The affected area is the back of the hand, leg, front of the torso, head or neck and arm. This image was taken at an angle.
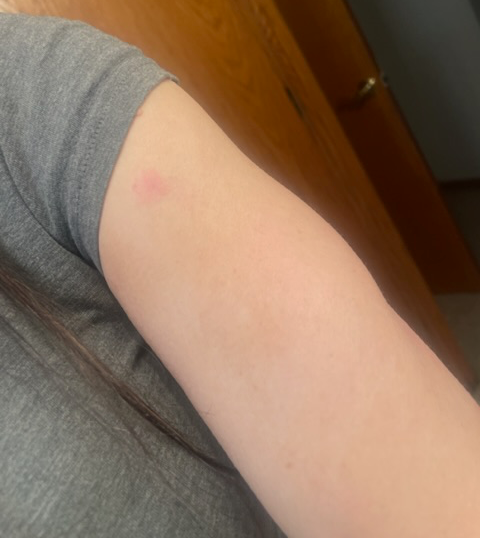The skin findings could not be characterized from the image. Texture is reported as flat and raised or bumpy. No associated systemic symptoms reported. The patient considered this skin that appeared healthy to them. Symptoms reported: enlargement, itching and bothersome appearance. Reported duration is one to four weeks.